The patient is a female in their mid-30s. A dermoscopic close-up of a skin lesion — 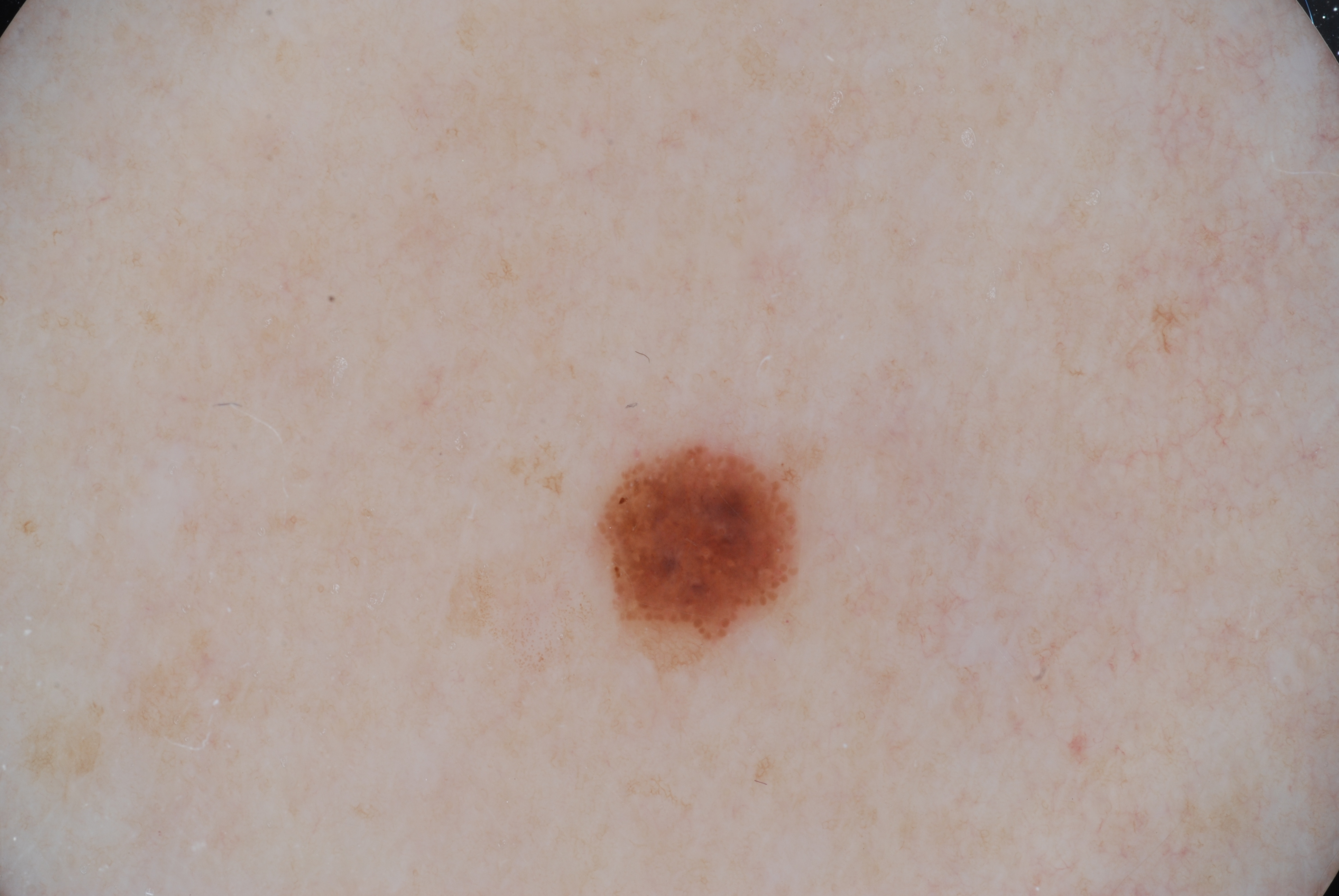Notes:
- location · x1=587 y1=437 x2=806 y2=673
- dermoscopic features assessed but absent · pigment network, milia-like cysts, negative network, and streaks
- impression · a melanocytic nevus, a benign skin lesion